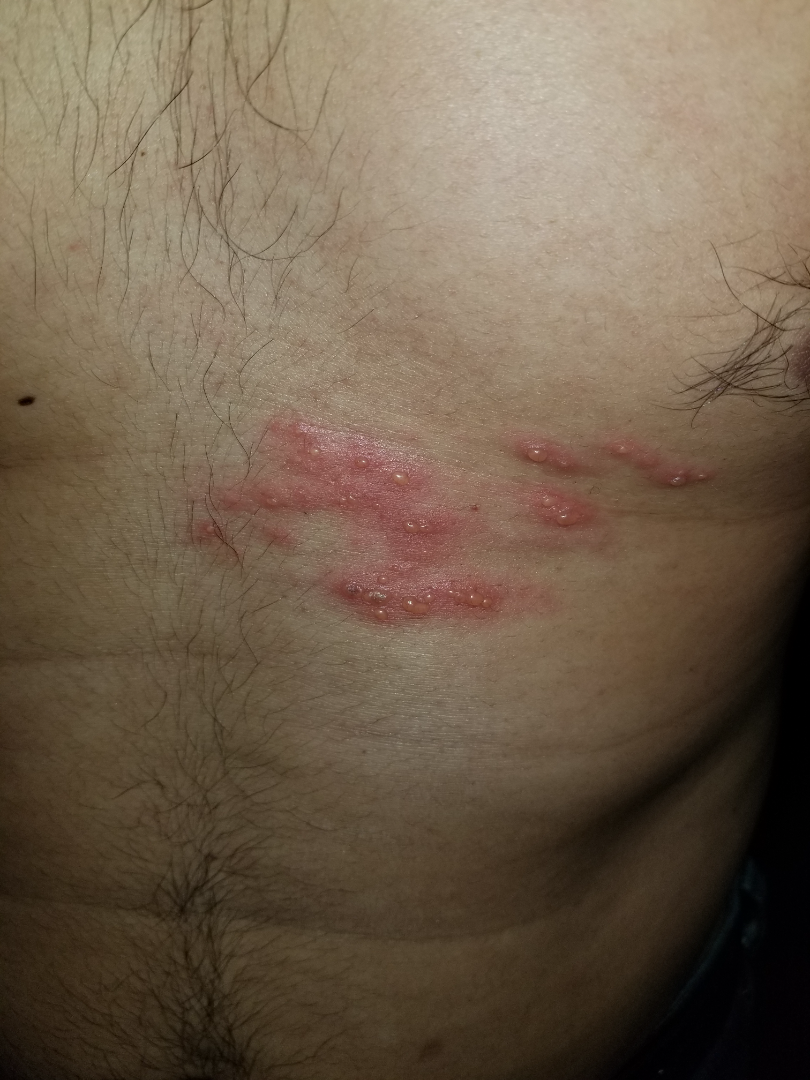present for = one to four weeks, view = close-up, lesion texture = raised or bumpy, constitutional symptoms = none reported, anatomic site = front of the torso, symptoms = itching, differential diagnosis = Herpes Zoster (primary).